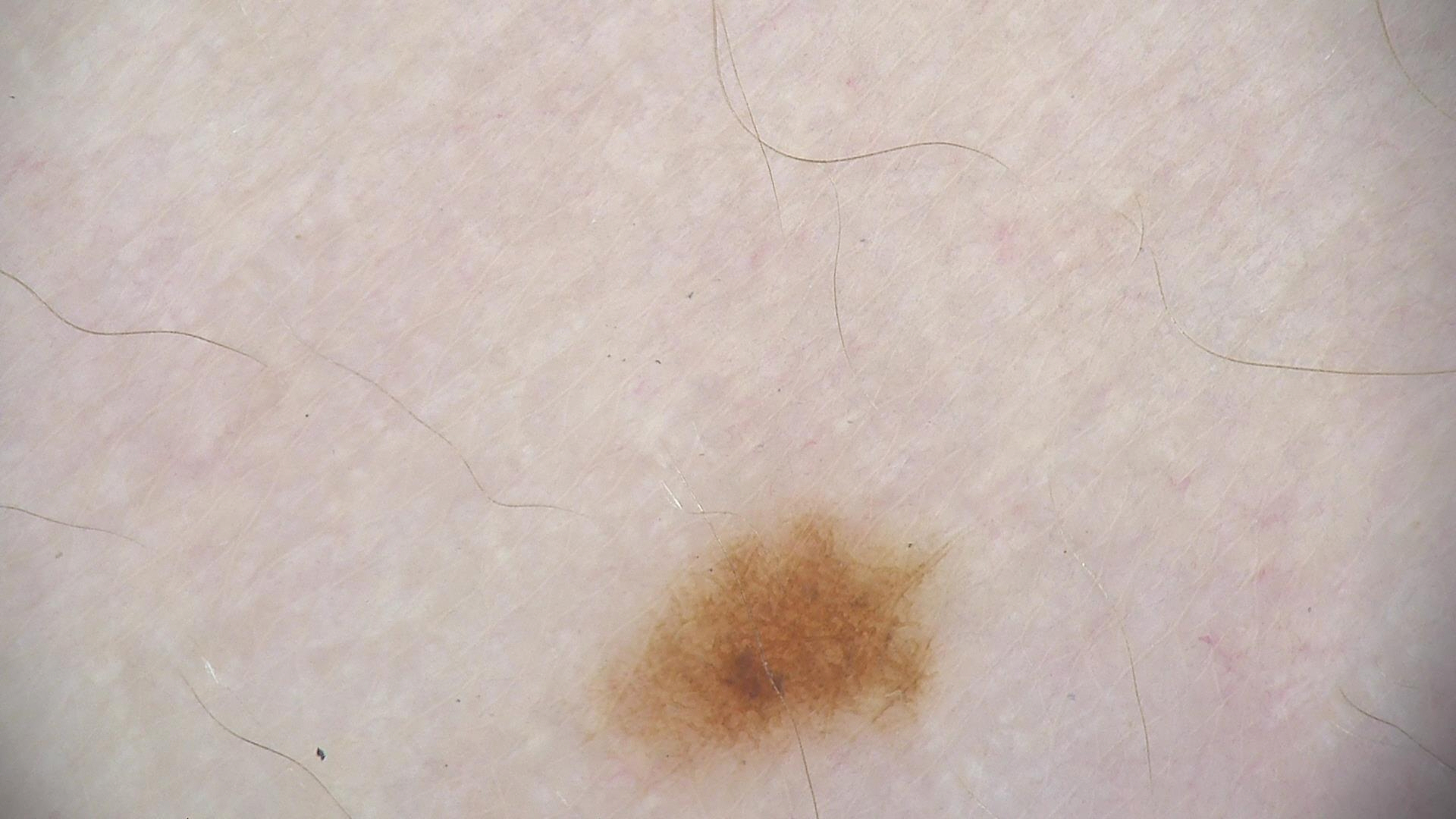Q: What is the imaging modality?
A: dermatoscopy
Q: What is this lesion?
A: dysplastic junctional nevus (expert consensus)